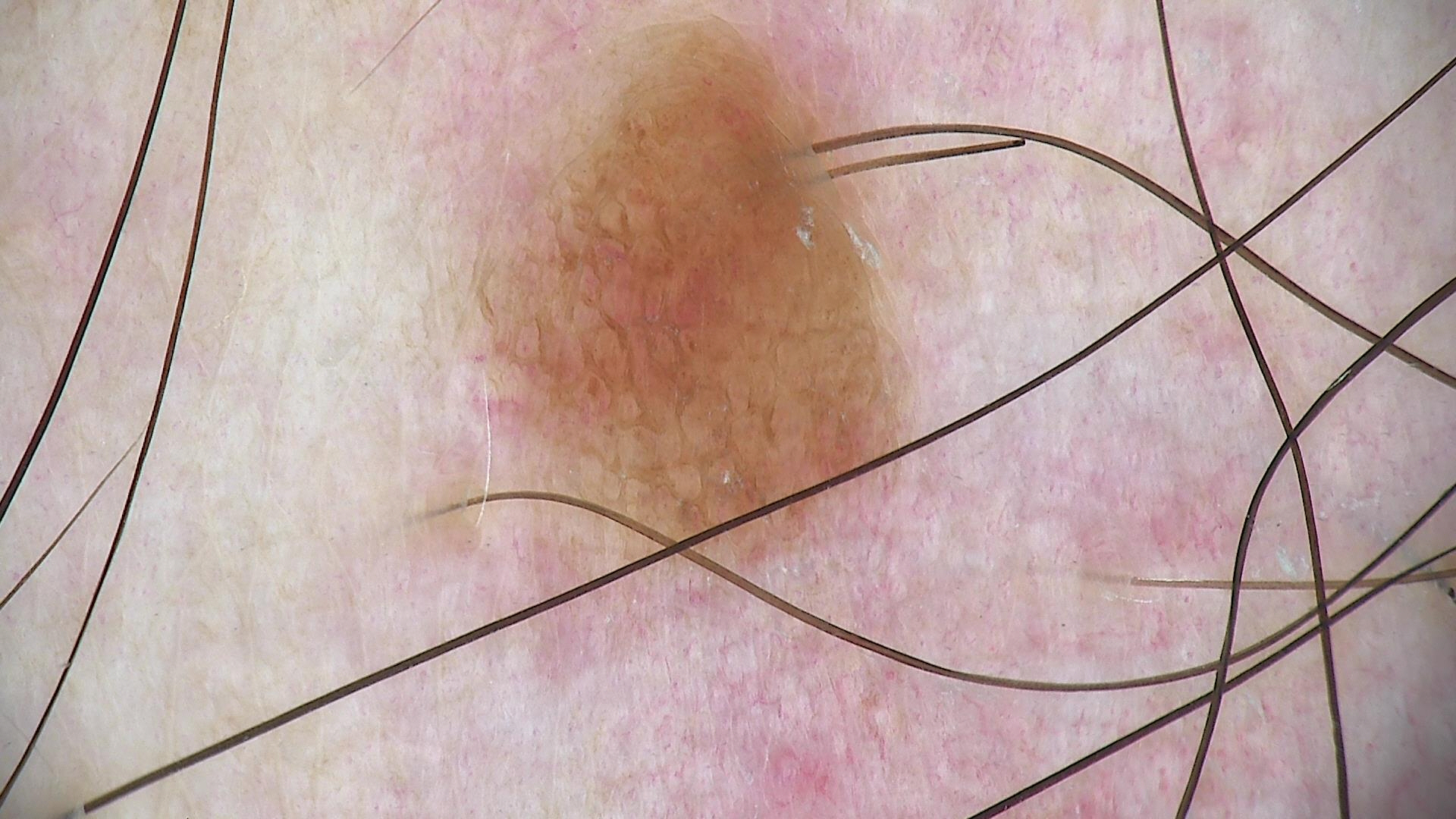imaging = dermatoscopy, category = banal, label = compound nevus (expert consensus).